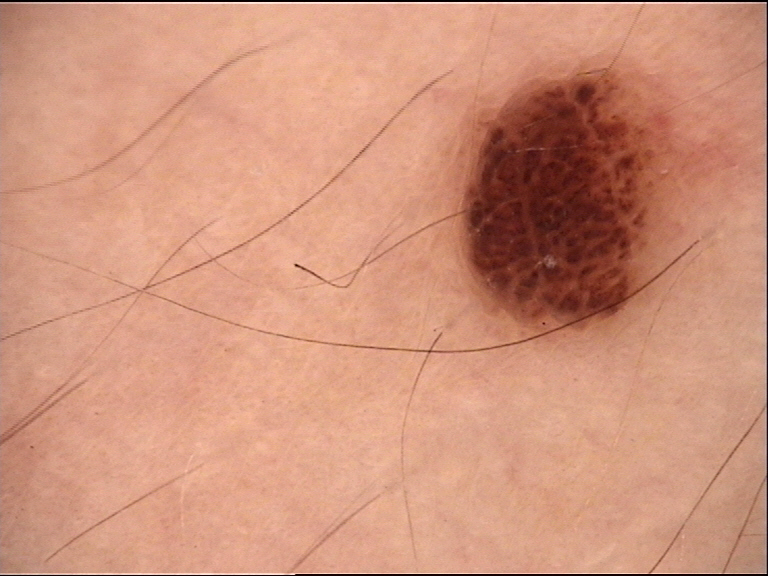Q: What kind of image is this?
A: dermoscopy
Q: What kind of lesion is this?
A: banal
Q: What is this lesion?
A: compound nevus (expert consensus)